A male patient aged 79 · a skin lesion imaged with a dermatoscope — 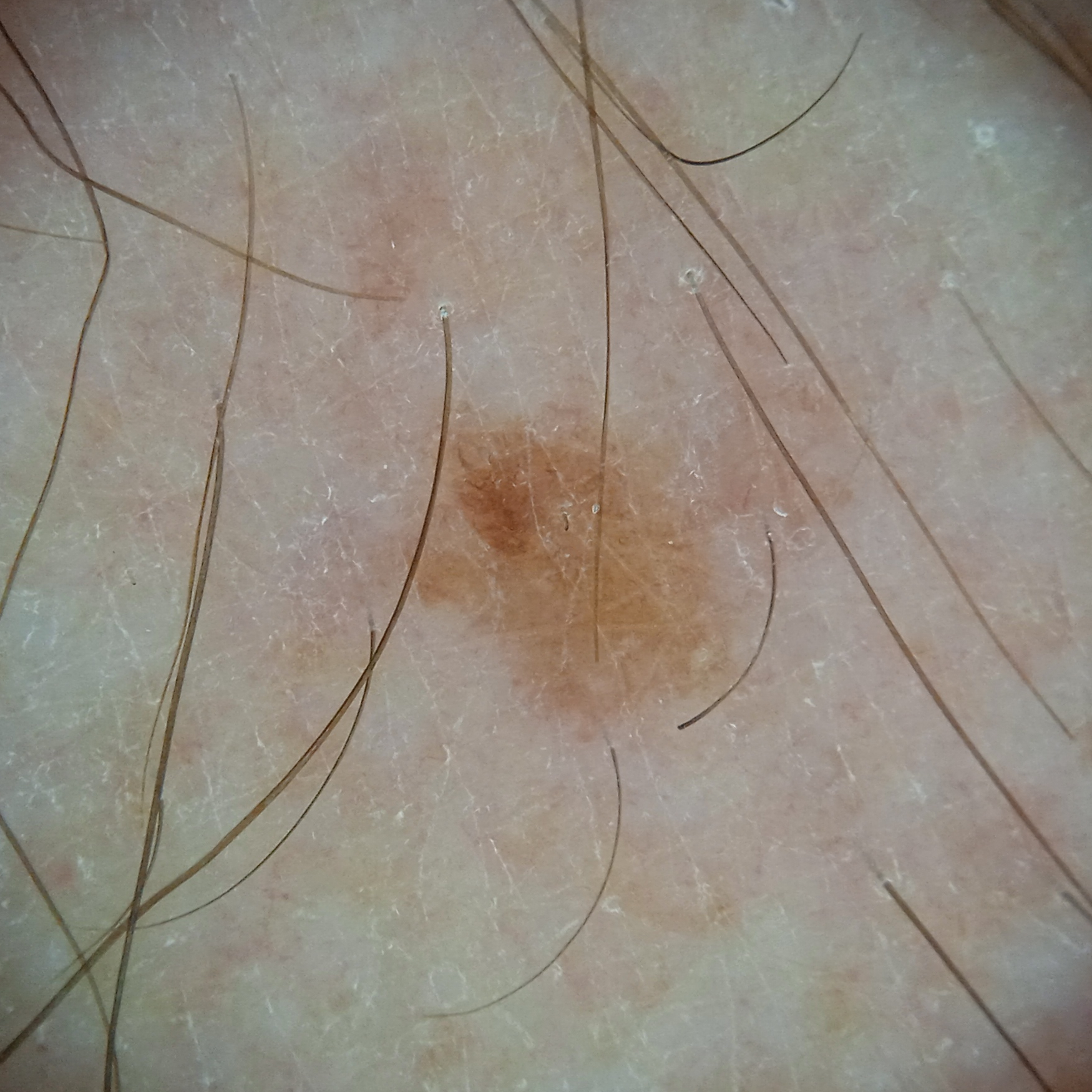anatomic site=an arm; size=4.2 mm; diagnostic label=seborrheic keratosis (dermatologist consensus).